A dermoscopic image of a skin lesion:
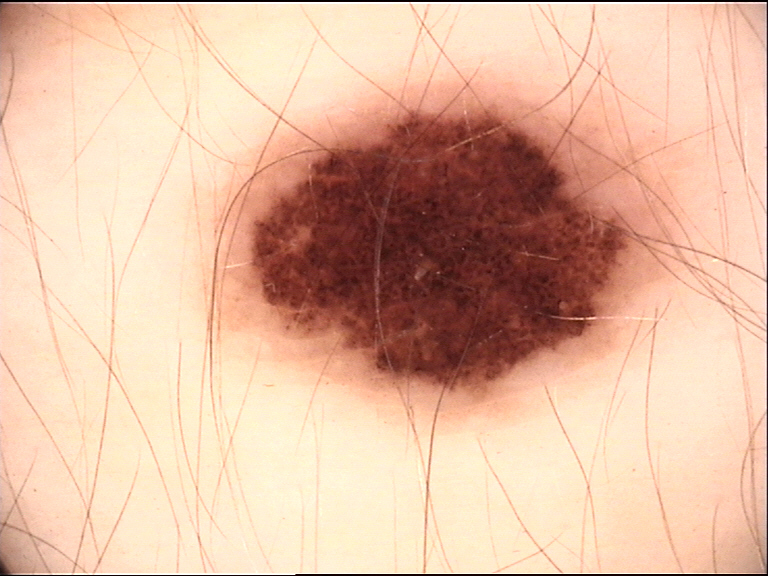  diagnosis:
    name: dysplastic junctional nevus
    code: jd
    malignancy: benign
    super_class: melanocytic
    confirmation: expert consensus